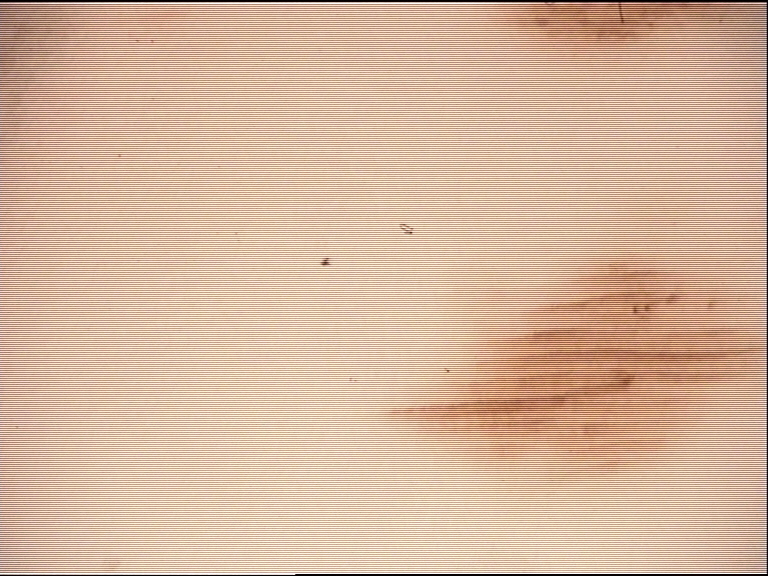A dermoscopic photograph of a skin lesion.
The diagnosis was a banal lesion — an acral junctional nevus.